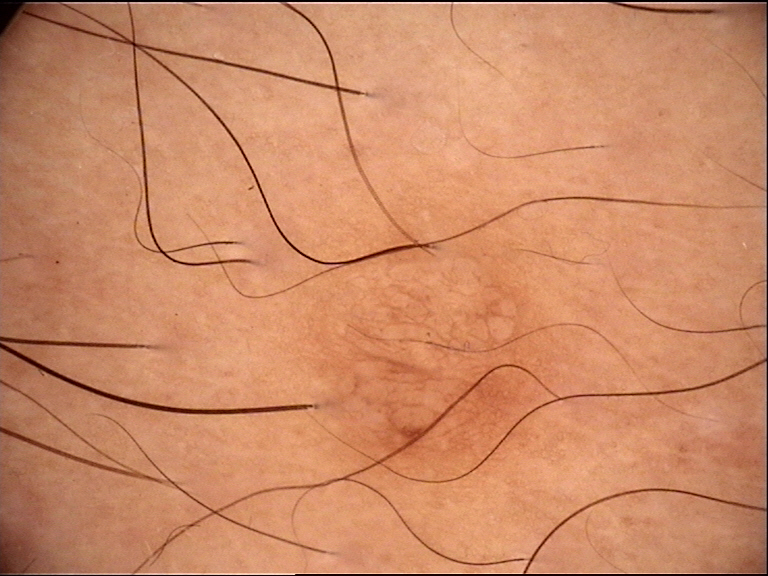Case:
A dermoscopic image of a skin lesion. The architecture is that of a banal lesion.
Impression:
Labeled as a dermal nevus.